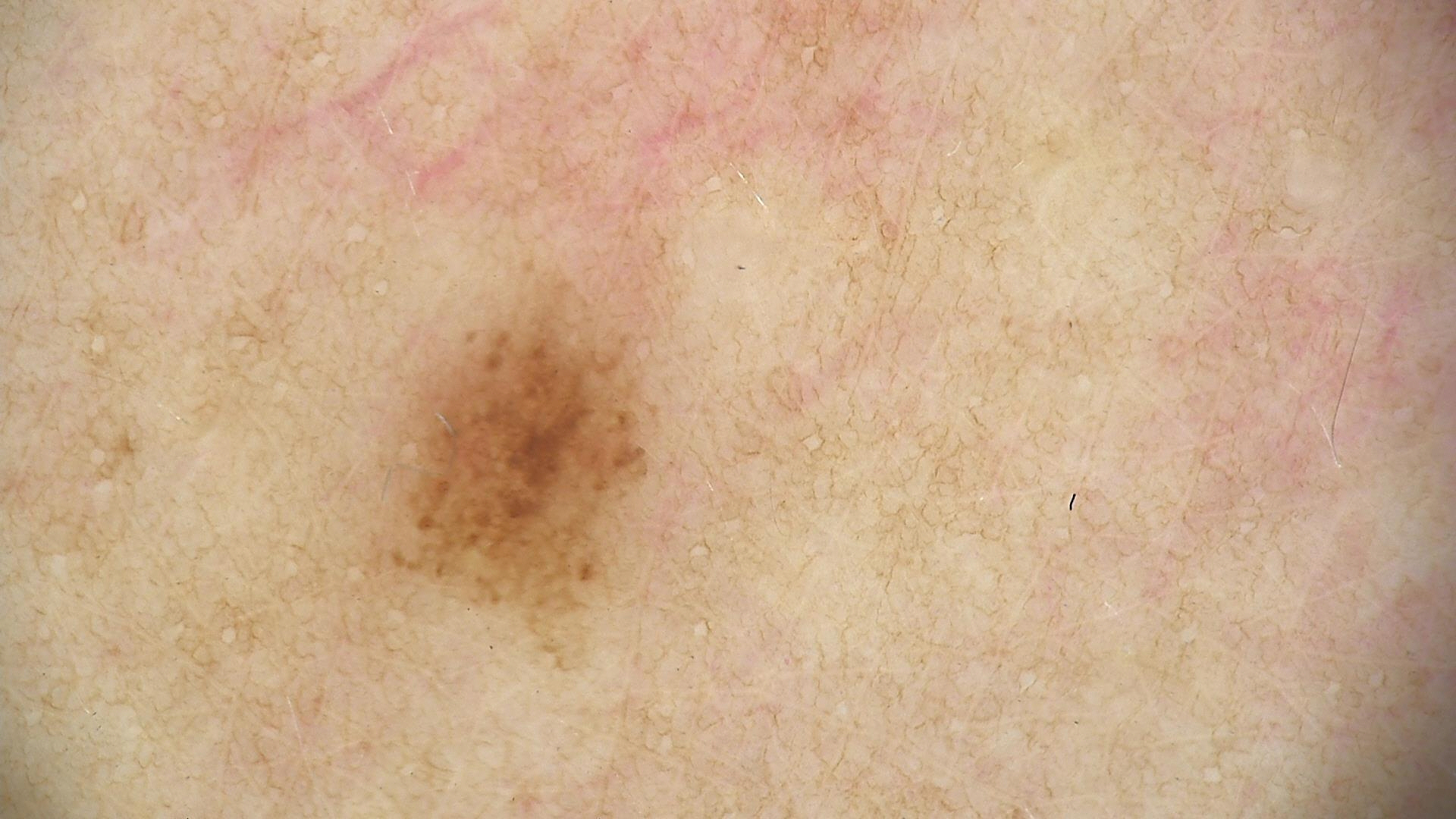imaging = dermatoscopy
label = dysplastic junctional nevus (expert consensus)